A dermoscopic close-up of a skin lesion: 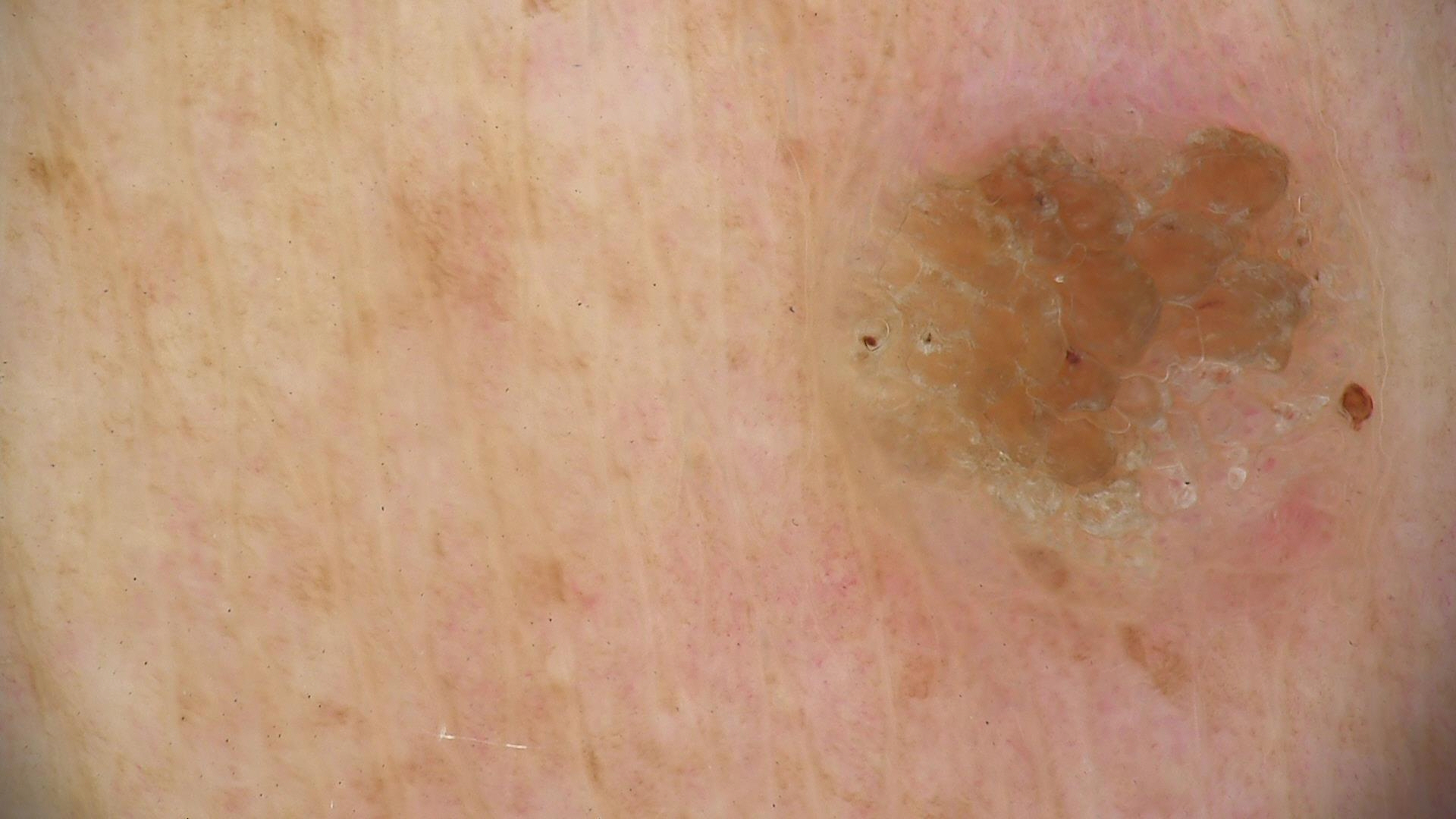Consistent with a benign, keratinocytic lesion — a seborrheic keratosis.